Dermoscopy of a skin lesion: 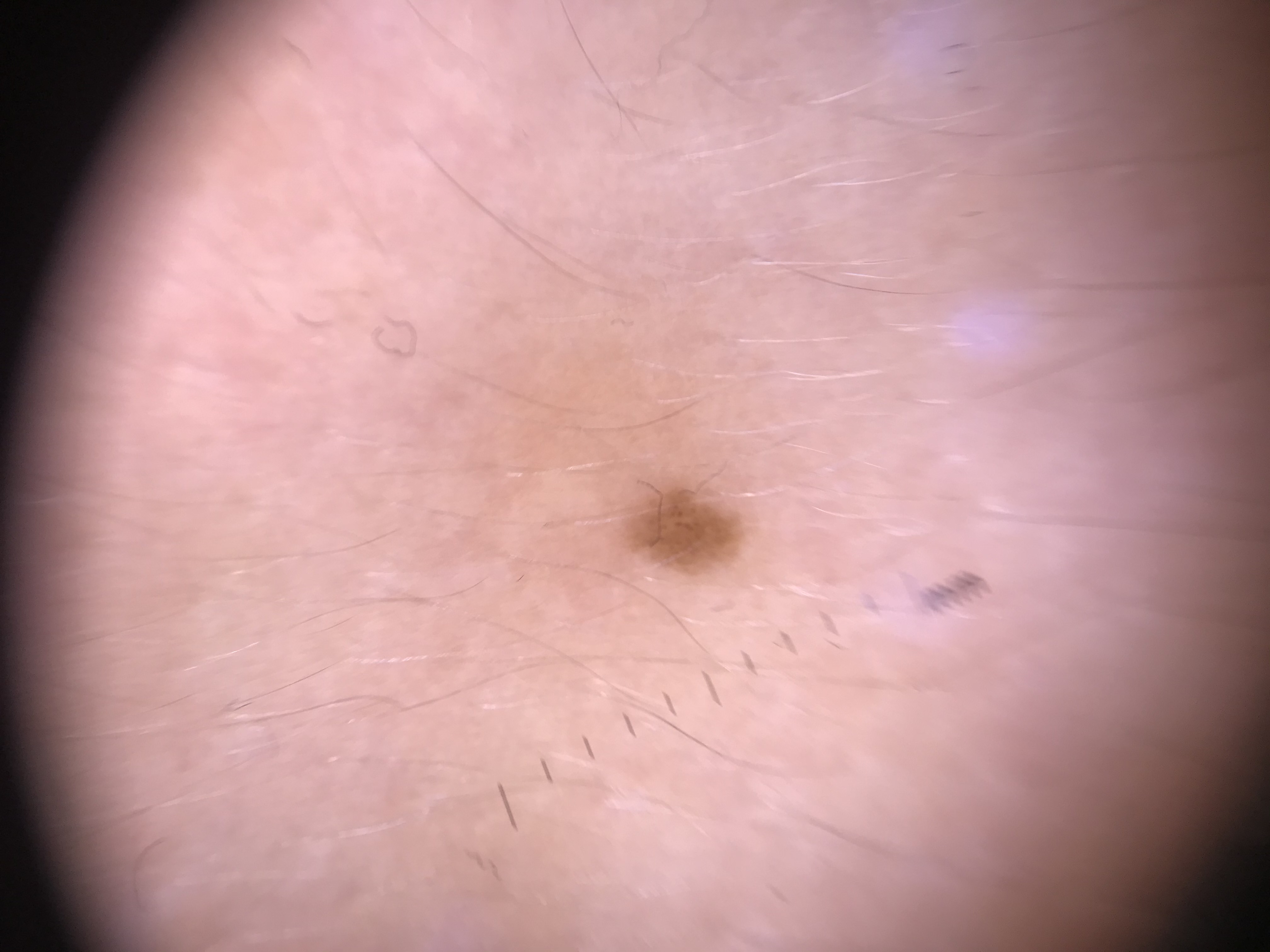Diagnosed as a banal lesion — a junctional nevus.